Close-up view.
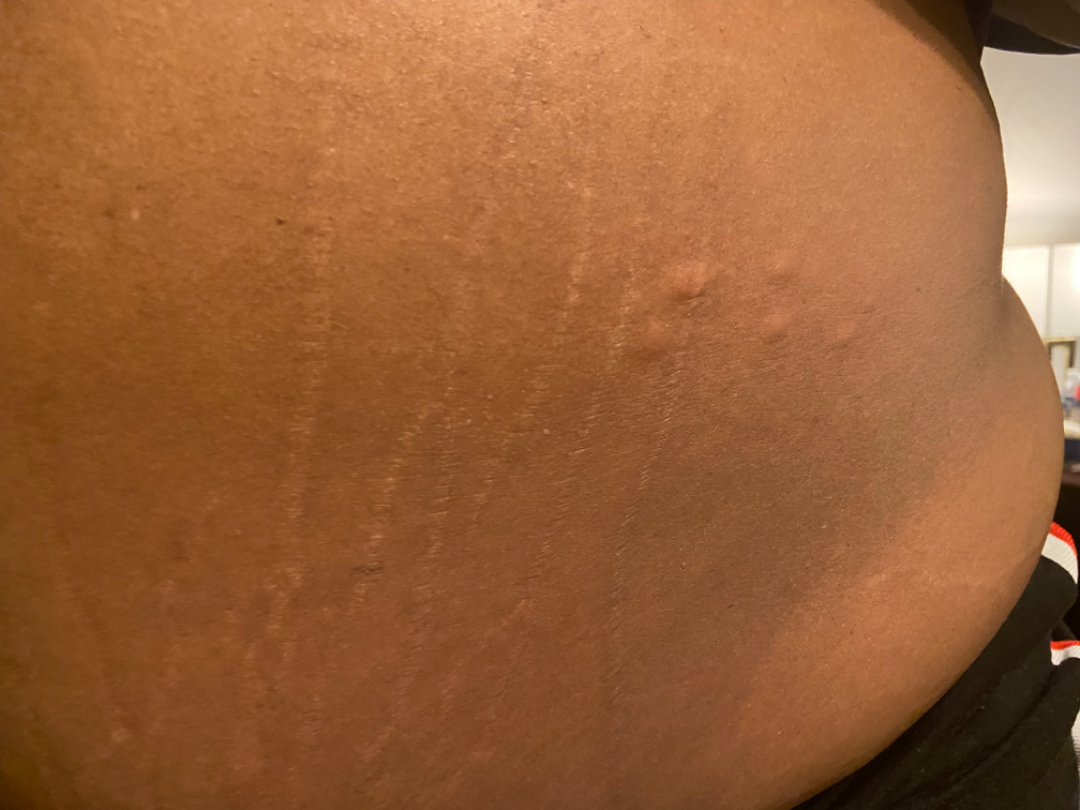The reviewing dermatologist was unable to assign a differential diagnosis from the image.